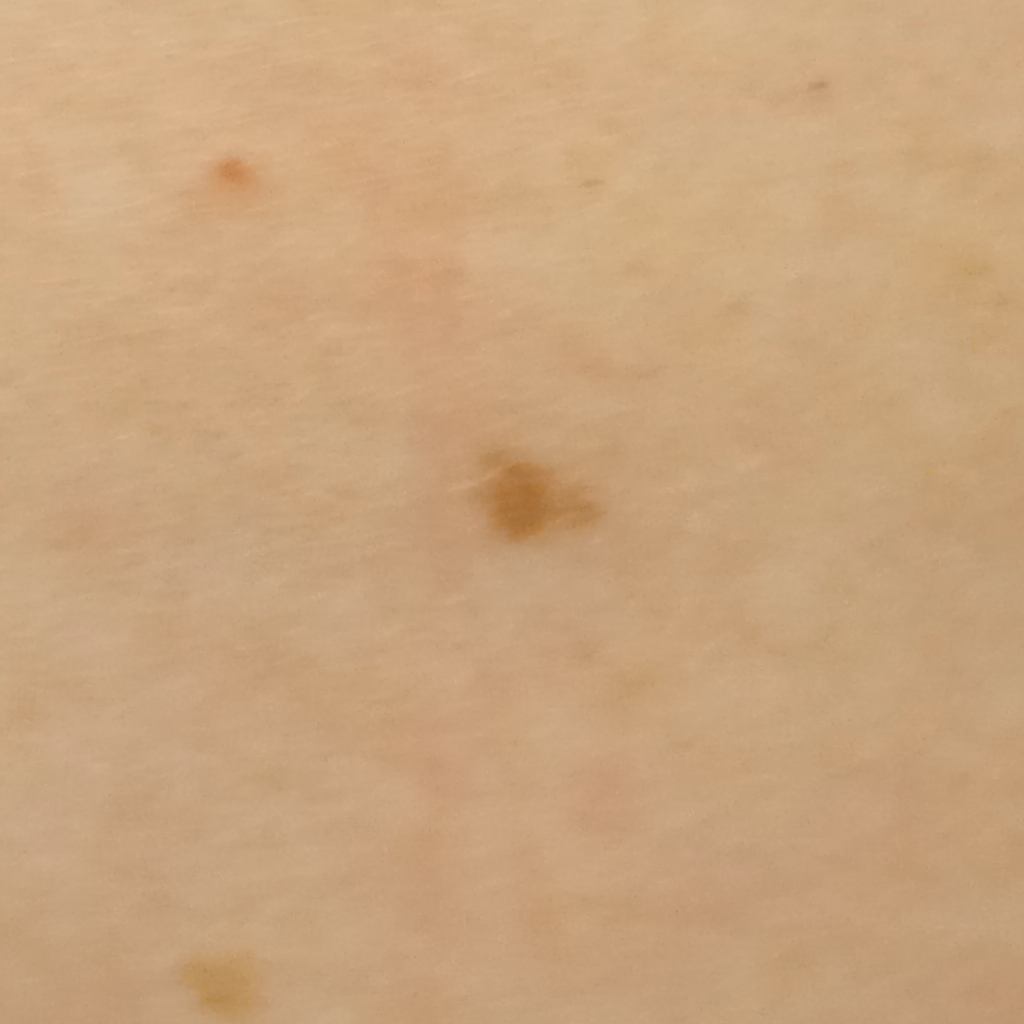Collected as part of a research study, without a referral diagnosis. A macroscopic clinical photograph of a skin lesion. The lesion is on the back. The consensus diagnosis for this lesion was a melanocytic nevus.